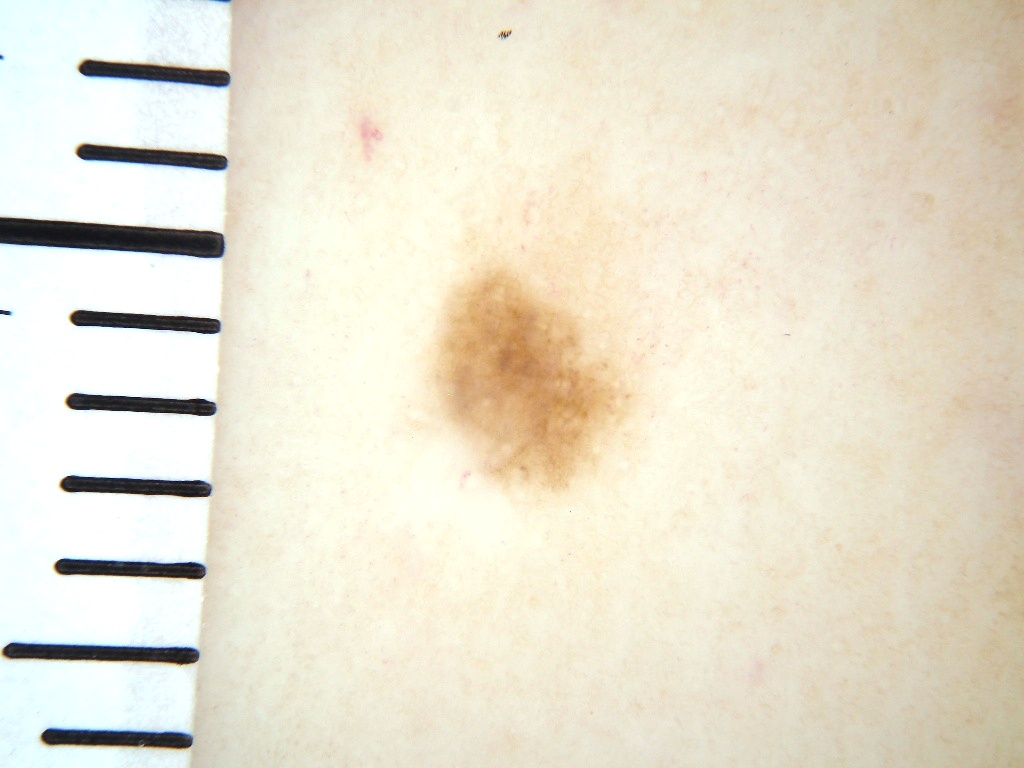{"patient": {"sex": "female", "age_approx": 40}, "image": {"modality": "dermoscopy"}, "lesion_location": {"bbox_xyxy": [431, 257, 632, 489]}, "lesion_extent": {"approx_field_fraction_pct": 4}, "dermoscopic_features": {"present": ["pigment network"], "absent": ["negative network", "globules", "streaks", "milia-like cysts"]}, "diagnosis": {"name": "melanocytic nevus", "malignancy": "benign", "lineage": "melanocytic", "provenance": "clinical"}}